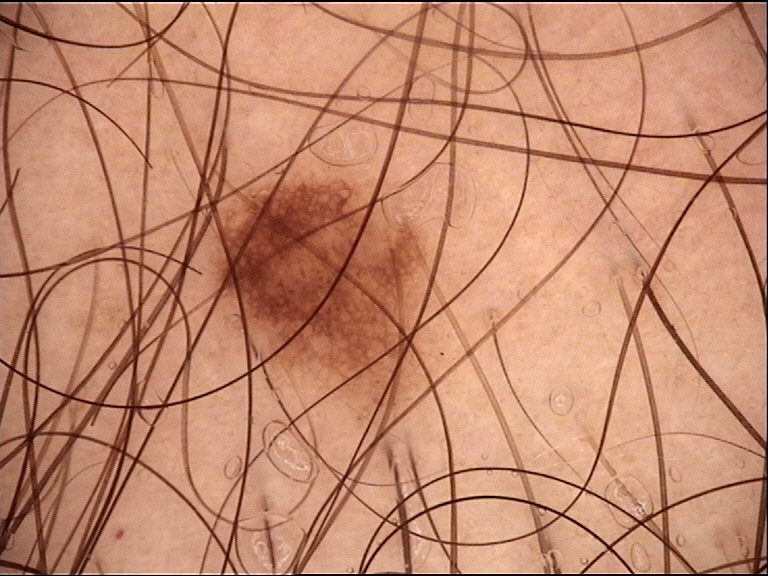{"image": "dermoscopy", "diagnosis": {"name": "dysplastic junctional nevus", "code": "jd", "malignancy": "benign", "super_class": "melanocytic", "confirmation": "expert consensus"}}